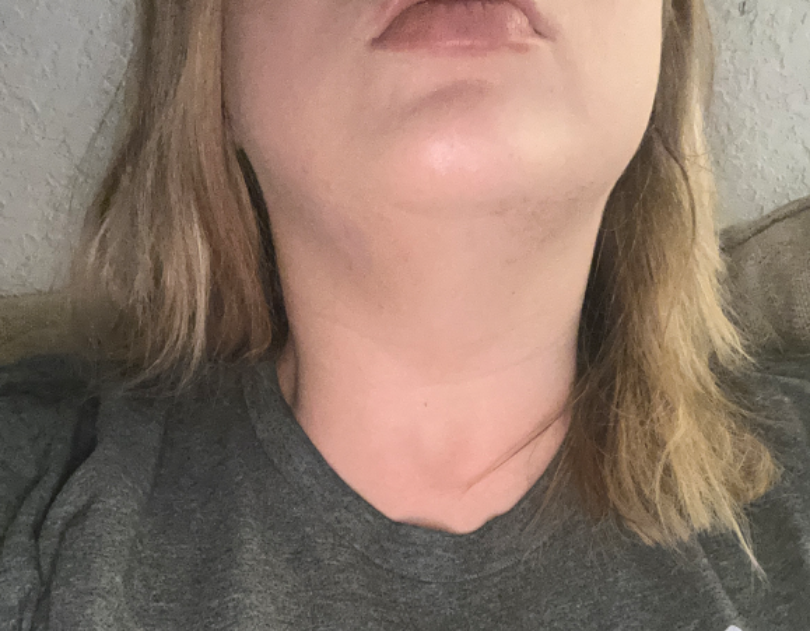Case summary:
• reported symptoms — bothersome appearance
• systemic symptoms — fatigue
• self-categorized as — a rash
• photo taken — at a distance
• surface texture — raised or bumpy
• patient — female, age 30–39
• body site — head or neck
• onset — less than one week
• clinical impression — most consistent with Acne